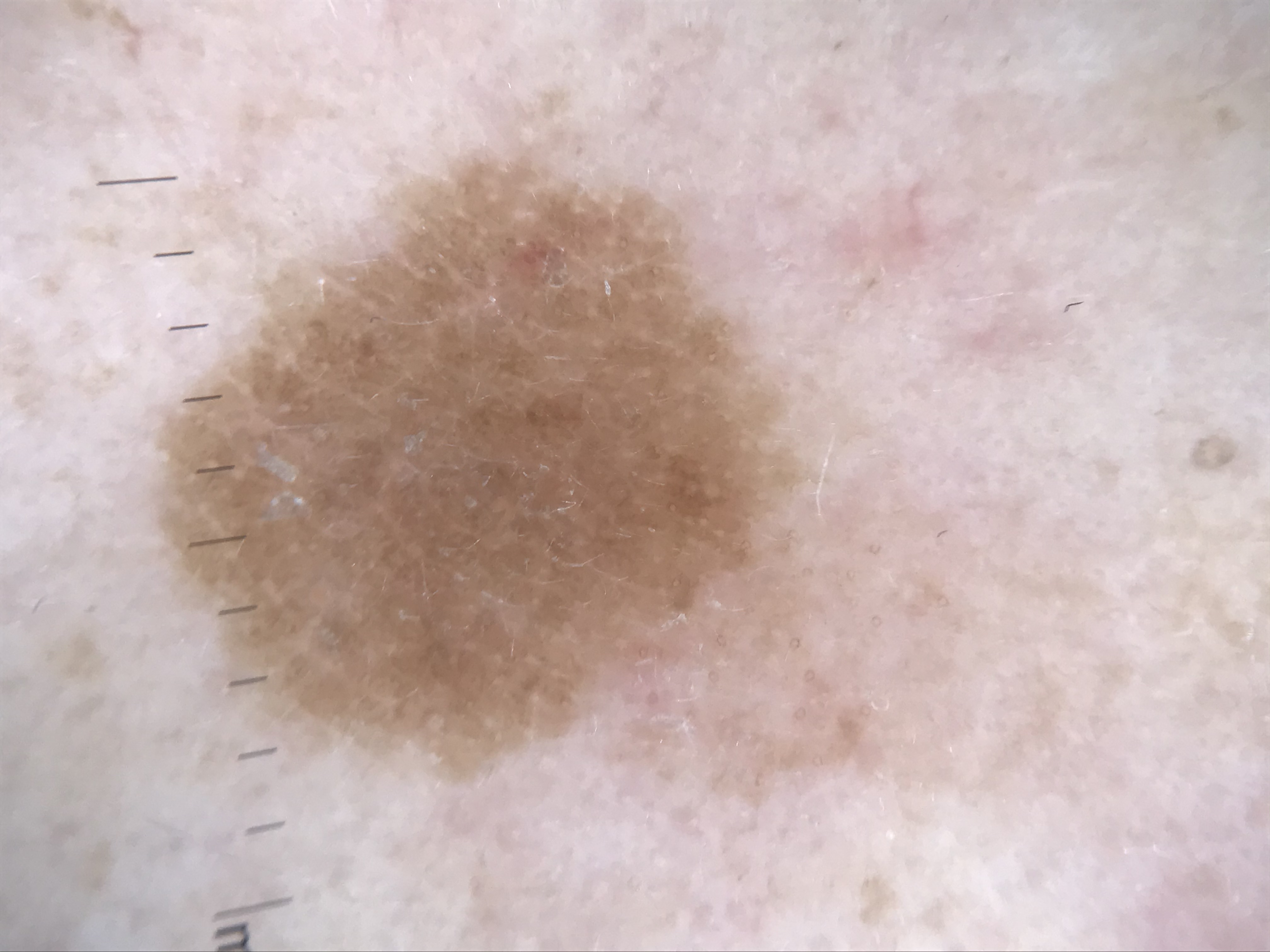The diagnostic label was a seborrheic keratosis.